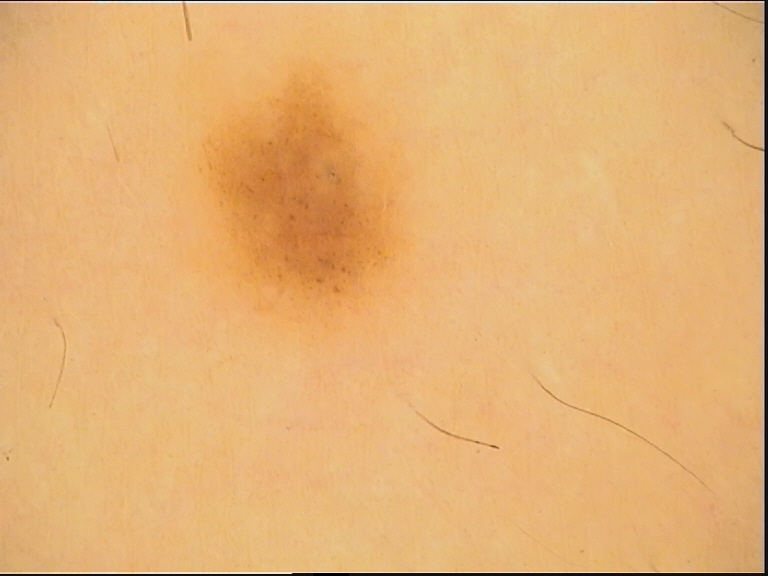label — dysplastic junctional nevus (expert consensus).